Imaged for a research study, with no referral diagnosis recorded. The patient says their skin reddens with sun exposure. A dermatoscopic image of a skin lesion. The patient describes having numerous moles. On a questionnaire the patient reported a history of sunbed use:
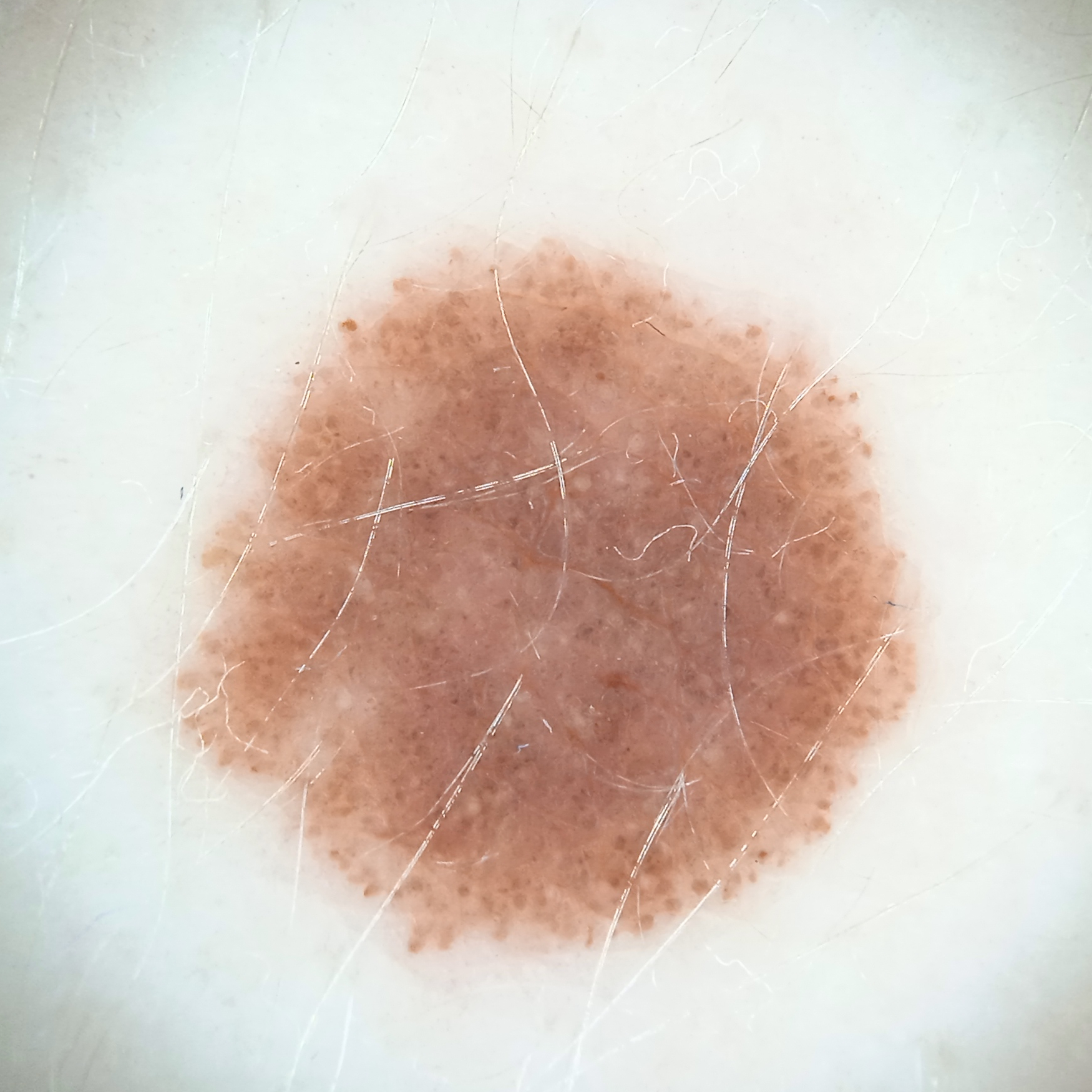{"lesion_location": "the back", "lesion_size": {"diameter_mm": 9.1}, "diagnosis": {"name": "melanocytic nevus", "malignancy": "benign"}}